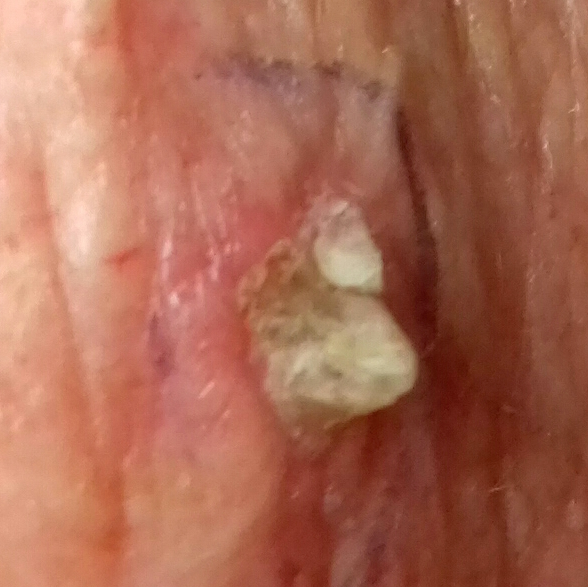Findings: A clinical photograph showing a skin lesion. A female subject 77 years of age. The lesion is on the chest. Conclusion: Confirmed on histopathology as a squamous cell carcinoma.